A skin lesion imaged with a dermatoscope: 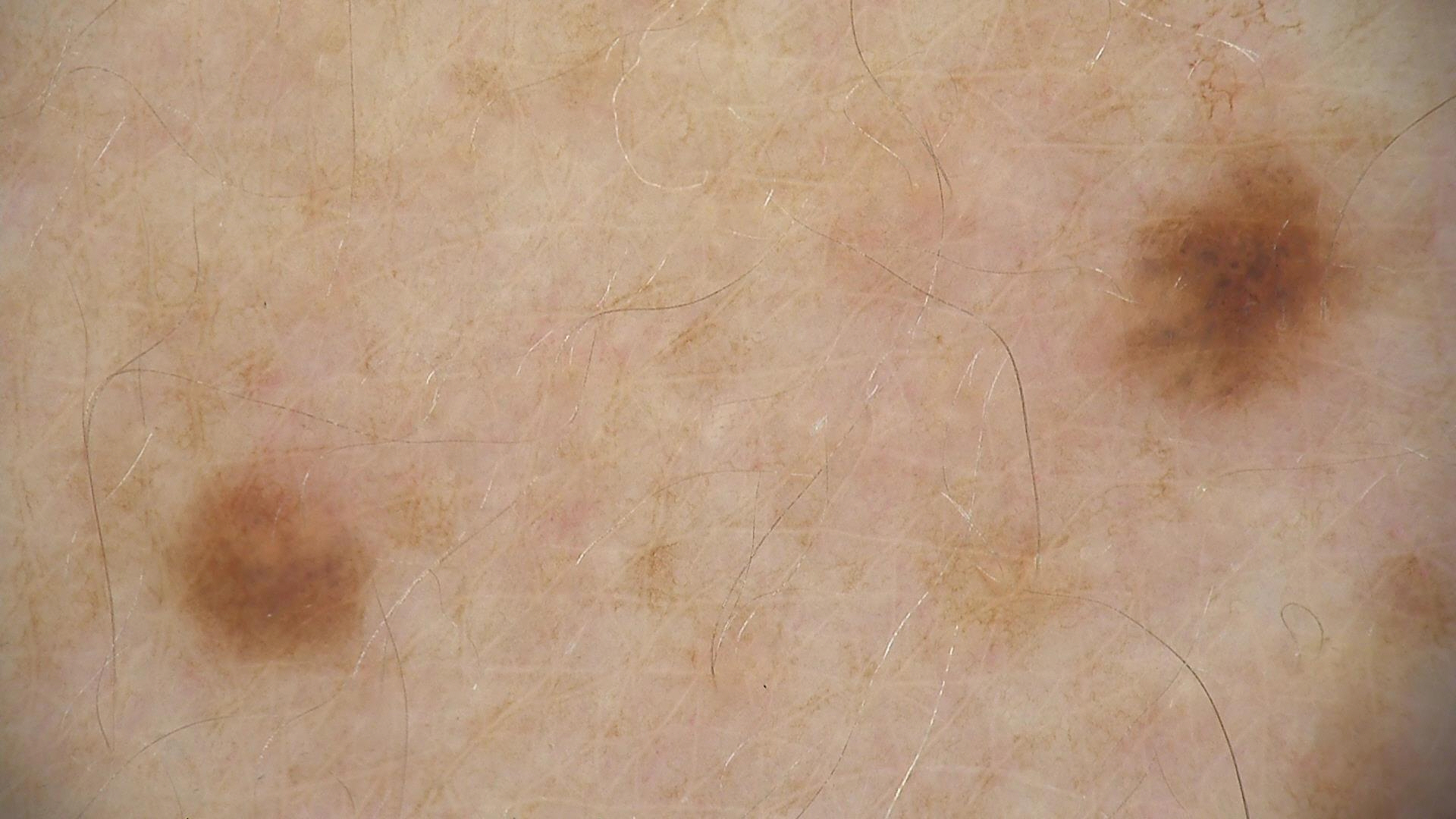Impression: The diagnostic label was a dysplastic junctional nevus.